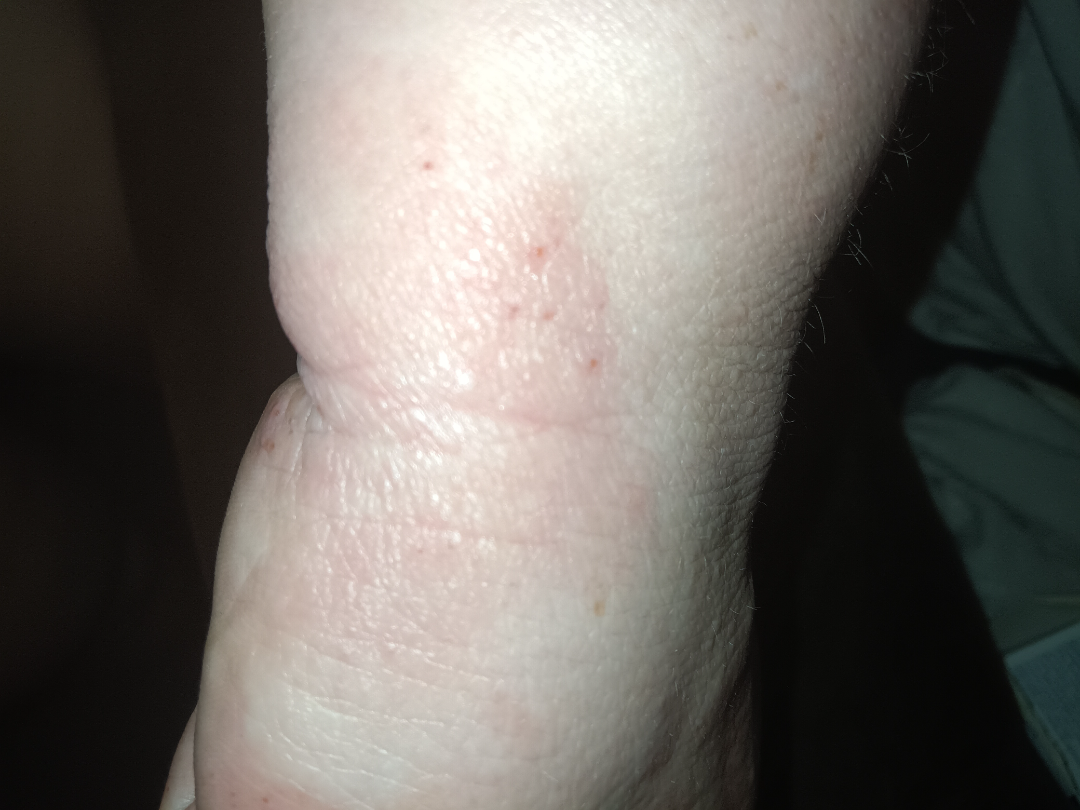Findings:
- onset — one to four weeks
- constitutional symptoms — none reported
- view — close-up
- location — palm and back of the hand
- lesion symptoms — itching
- surface texture — raised or bumpy
- differential diagnosis — reviewed remotely by one dermatologist: most consistent with Eczema; also raised was Lichen Simplex Chronicus